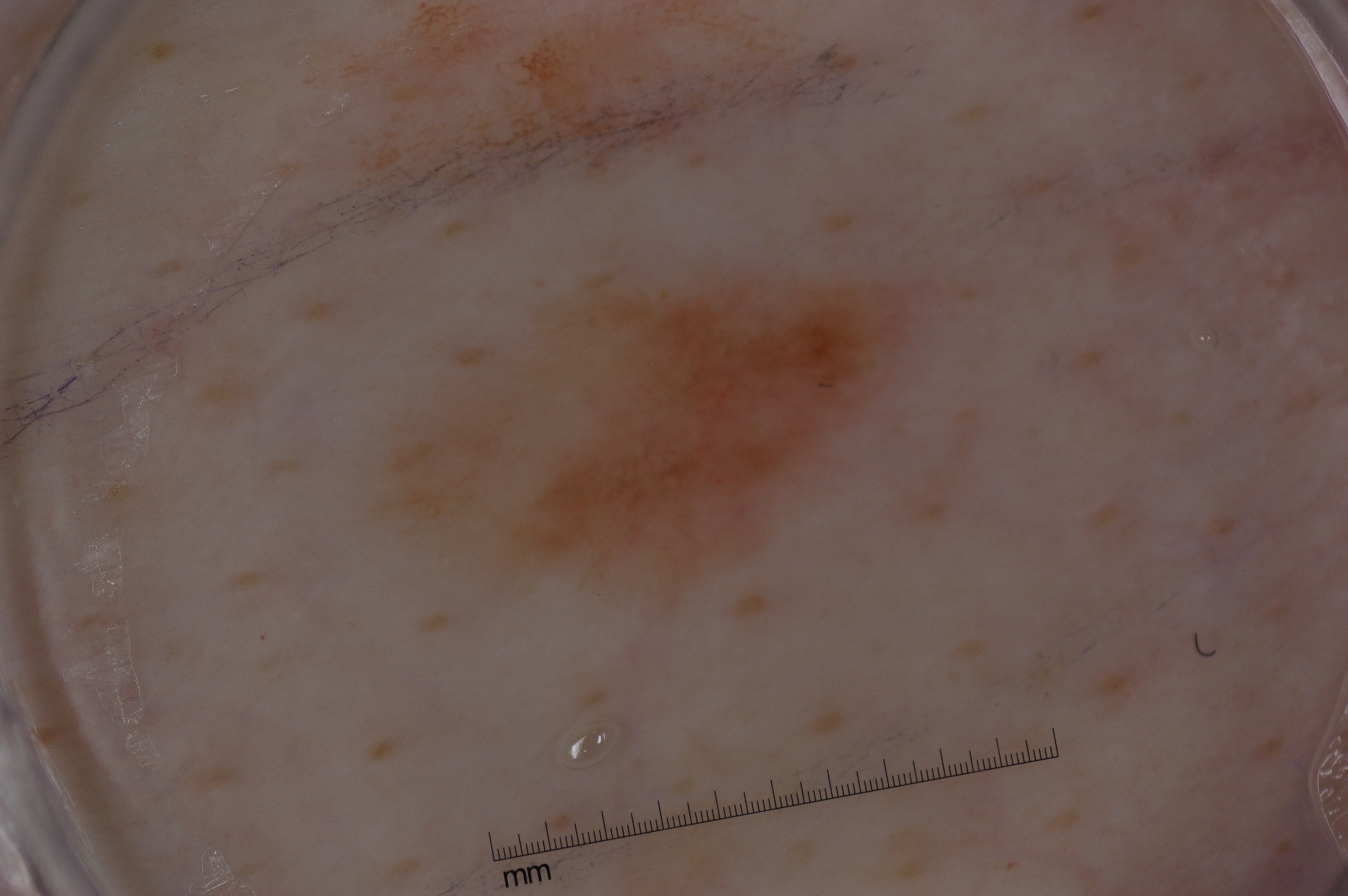image: dermoscopy of a skin lesion | patient: male, aged around 40 | lesion location: (378, 272, 909, 610) | lesion size: moderate | absent dermoscopic findings: streaks, negative network, pigment network, and milia-like cysts | impression: a melanocytic nevus, a benign lesion.